The patient is a female aged 18–29. The photograph was taken at a distance. The affected area is the leg, head or neck and arm: 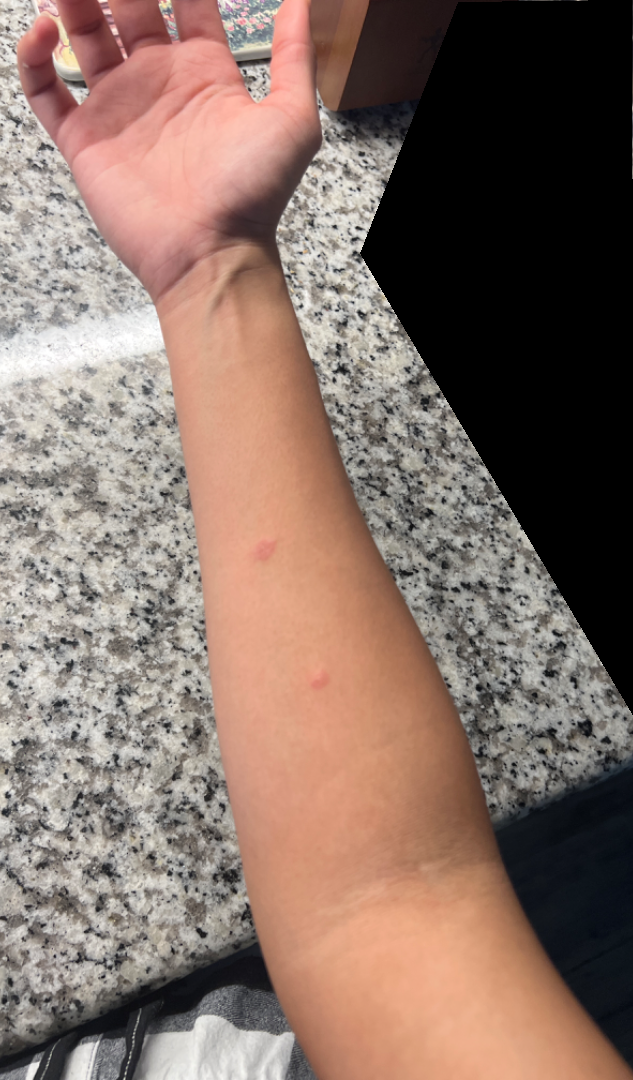On remote review of the image: the impression on review was Insect Bite.